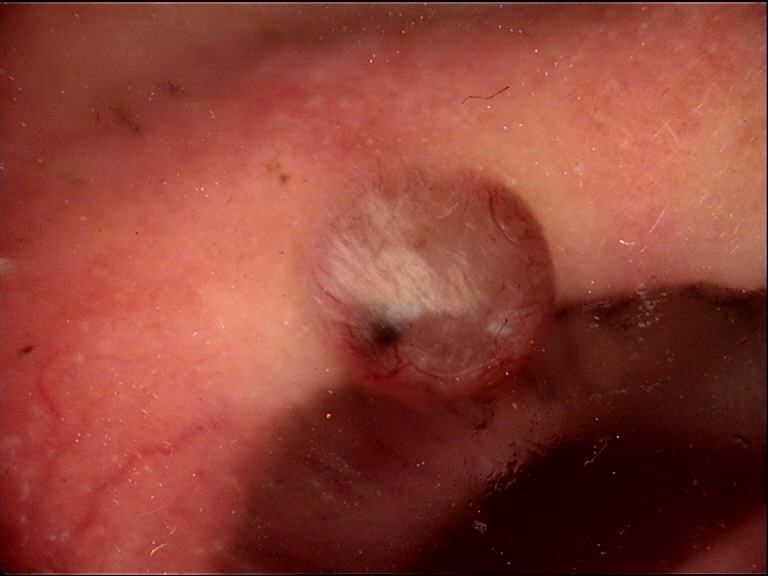A skin lesion imaged with a dermatoscope. This is a keratinocytic lesion. Biopsy-confirmed as a skin cancer — a basal cell carcinoma.